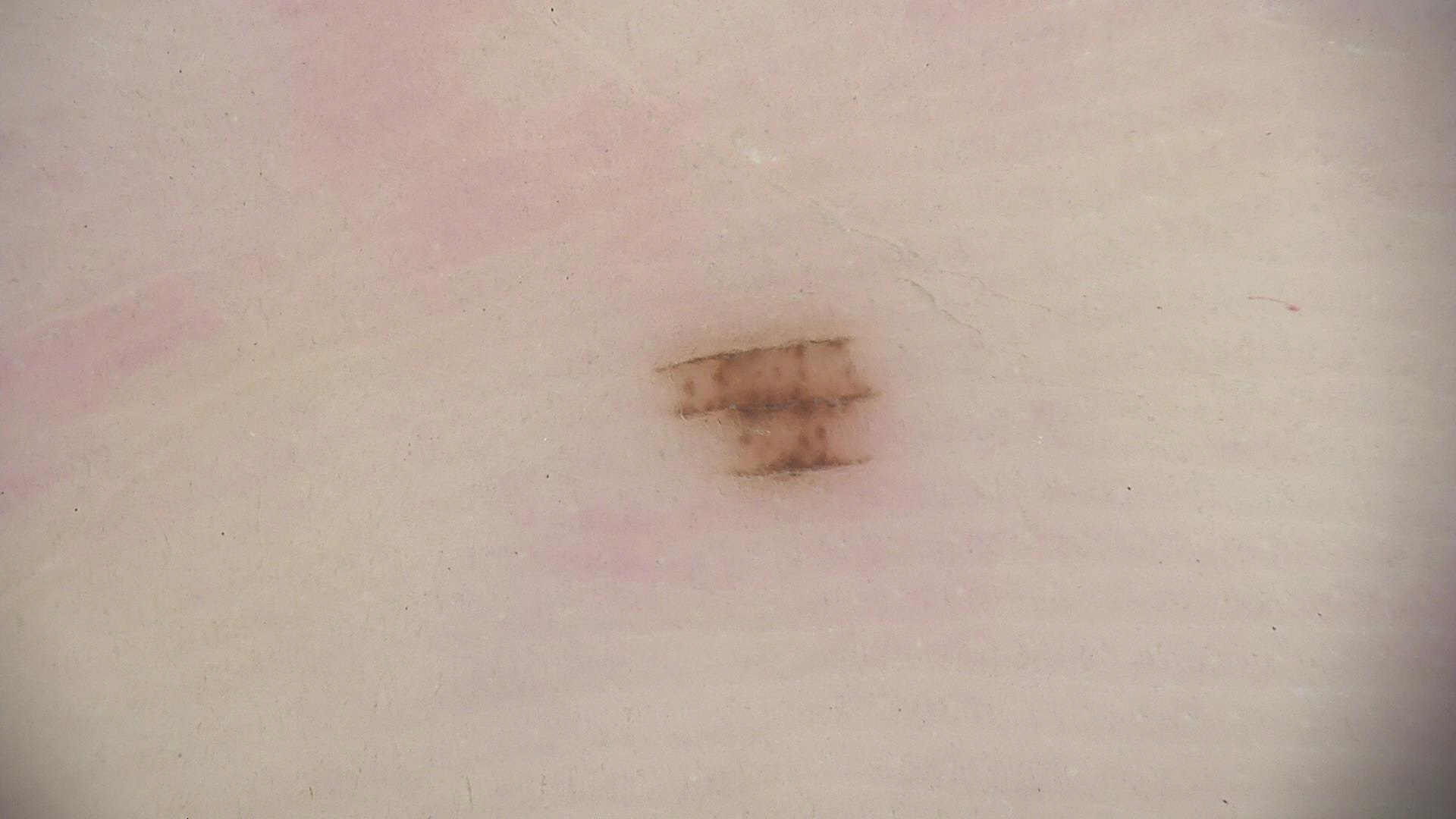Conclusion:
The diagnosis was an acral dysplastic junctional nevus.